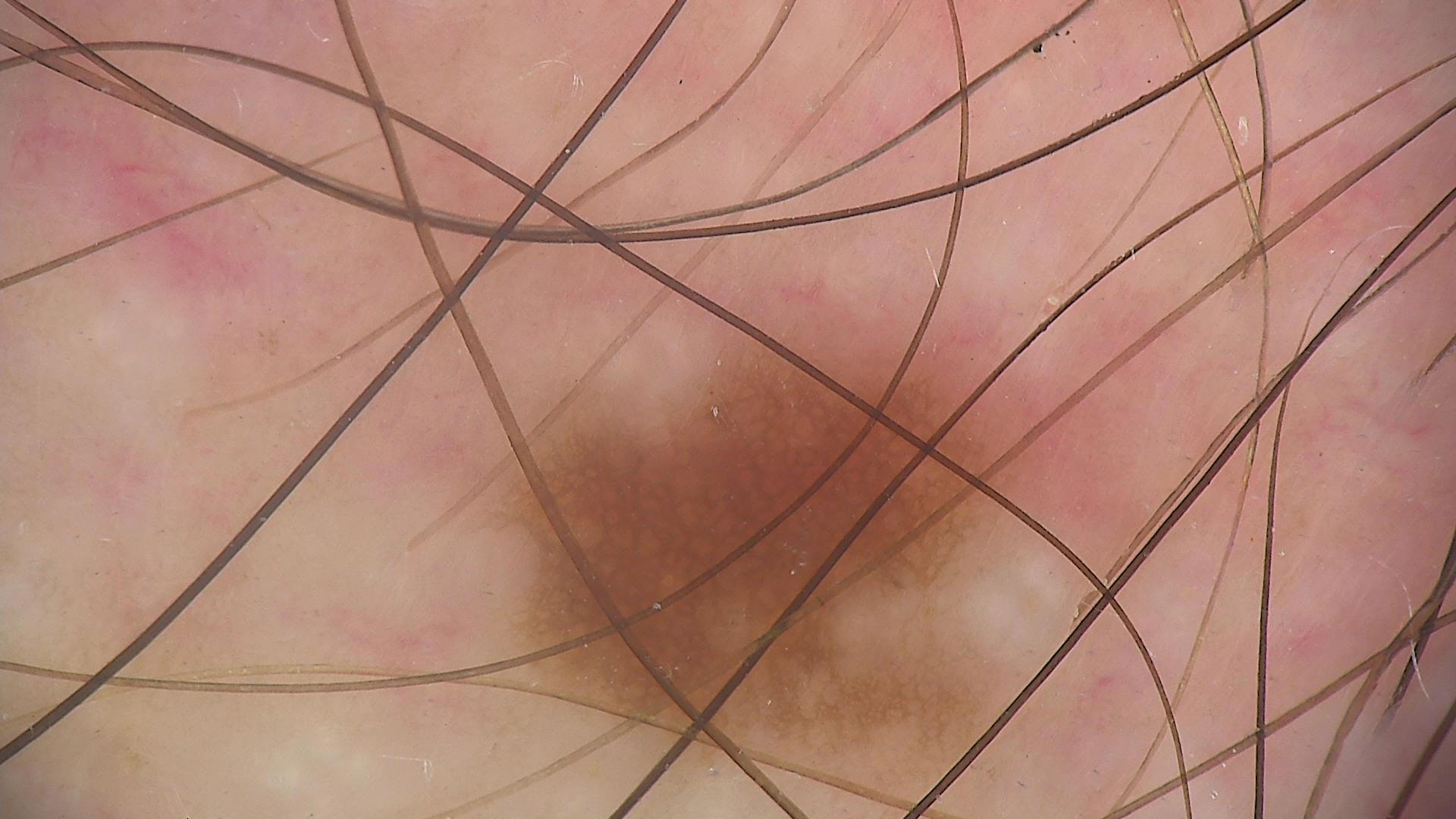The diagnostic label was a benign lesion — a dysplastic junctional nevus.